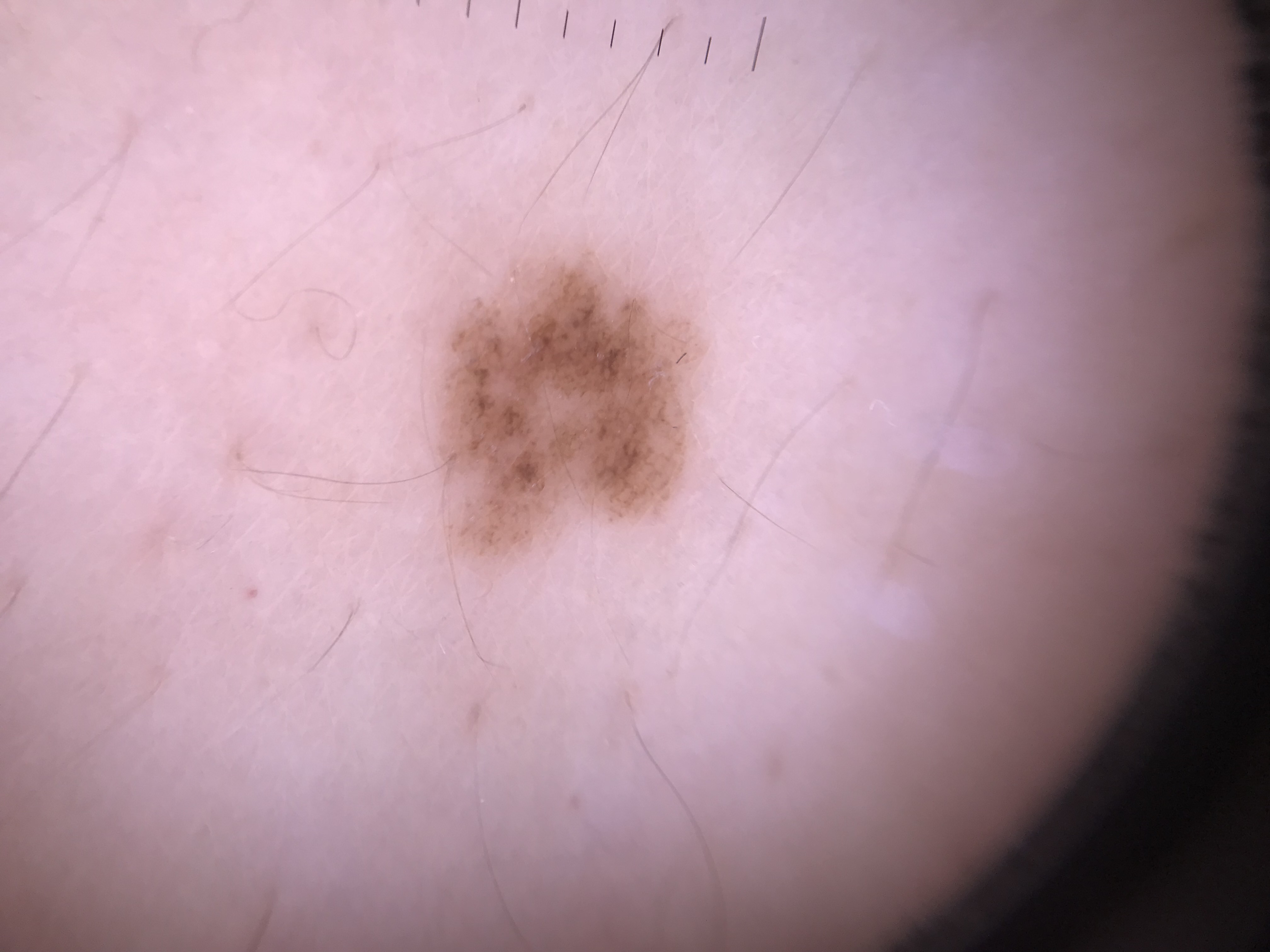diagnosis: dysplastic junctional nevus (expert consensus).